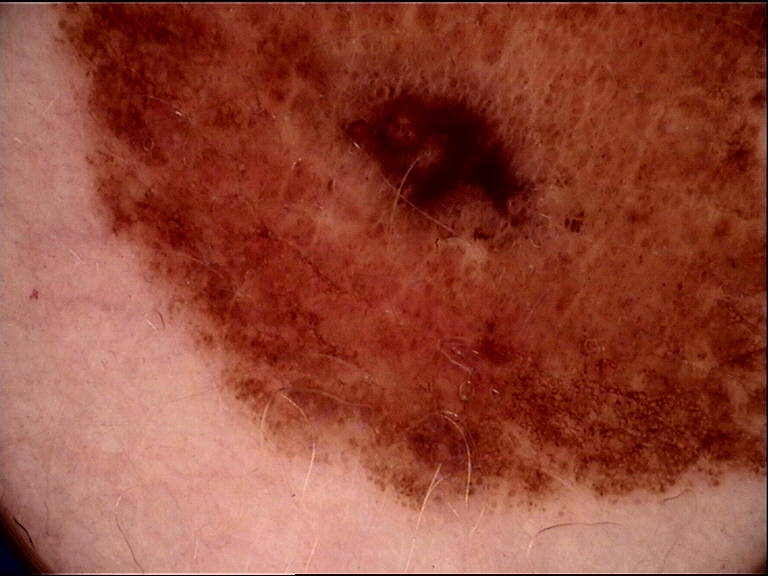A dermoscopic close-up of a skin lesion.
The morphology is that of a banal lesion.
The diagnosis was a congenital compound nevus.